The patient is skin type II · an overview clinical photograph of a skin lesion · a female subject roughly 85 years of age or older.
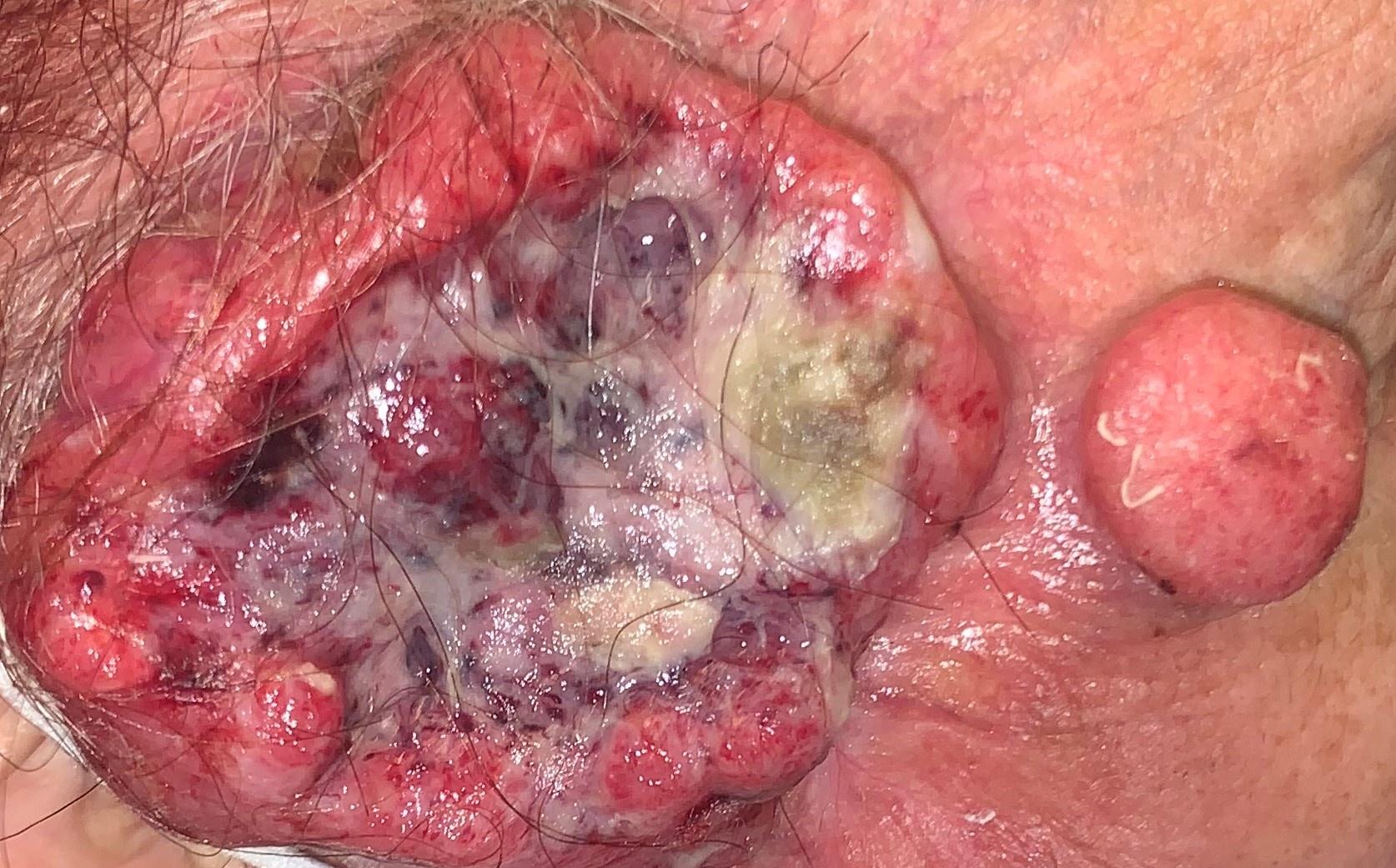Histopathology confirmed a malignancy — a squamous cell carcinoma.